The photograph was taken at an angle · the subject is 18–29, male: 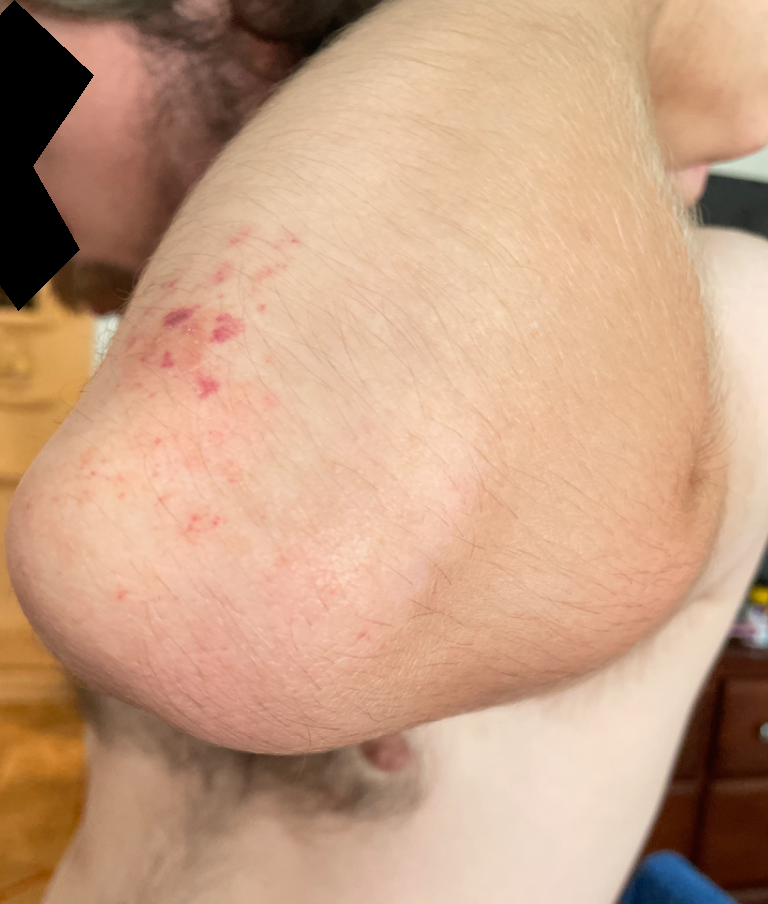* impression: Contact dermatitis (possible); Purpura (possible); Pigmented purpuric eruption (unlikely); ecchymoses (unlikely)